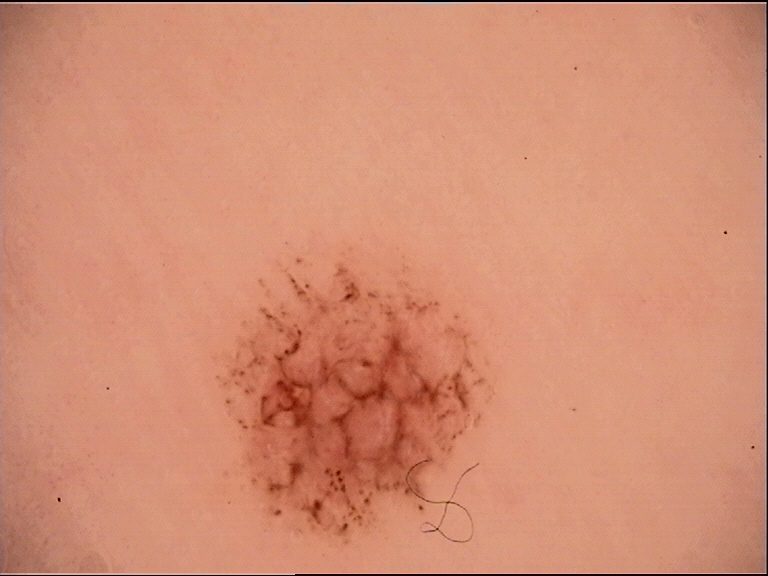A dermoscopic image of a skin lesion. Consistent with an acral dysplastic junctional nevus.